The photograph is a close-up of the affected area:
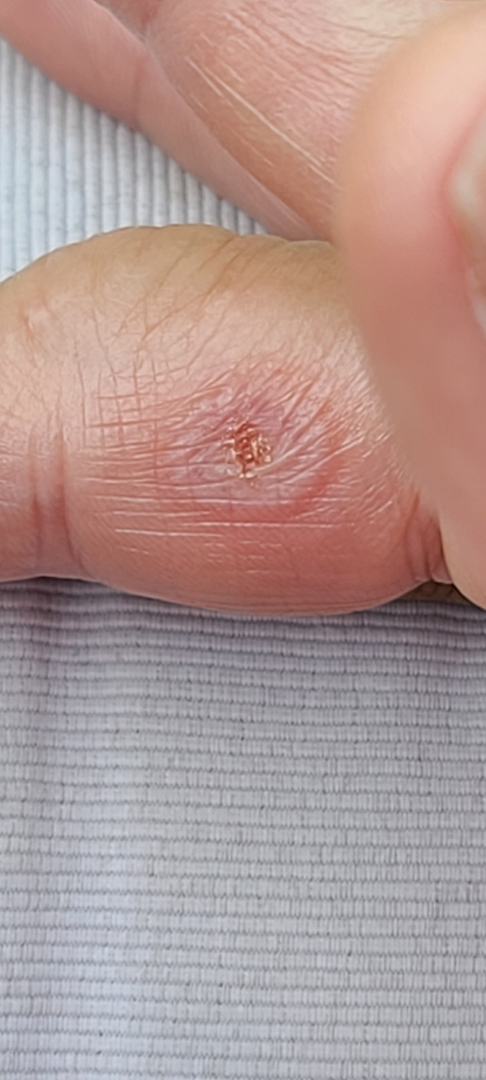{"differential": {"leading": ["Insect Bite"], "considered": ["Erythema multiforme", "Burn of skin"]}}